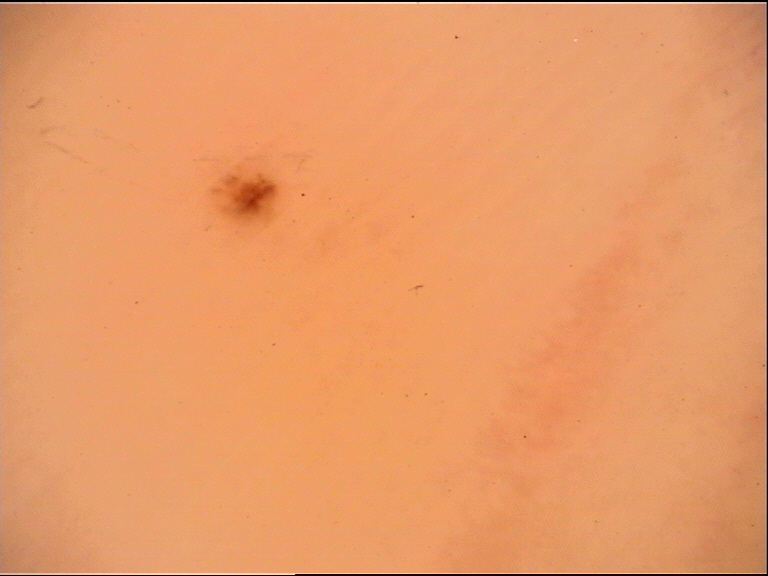The morphology is that of a banal lesion.
Consistent with an acral junctional nevus.